The photograph was taken at an angle · the lesion is associated with pain, burning and itching · texture is reported as raised or bumpy and rough or flaky · the patient indicates the condition has been present for one to four weeks · the affected area is the back of the hand: 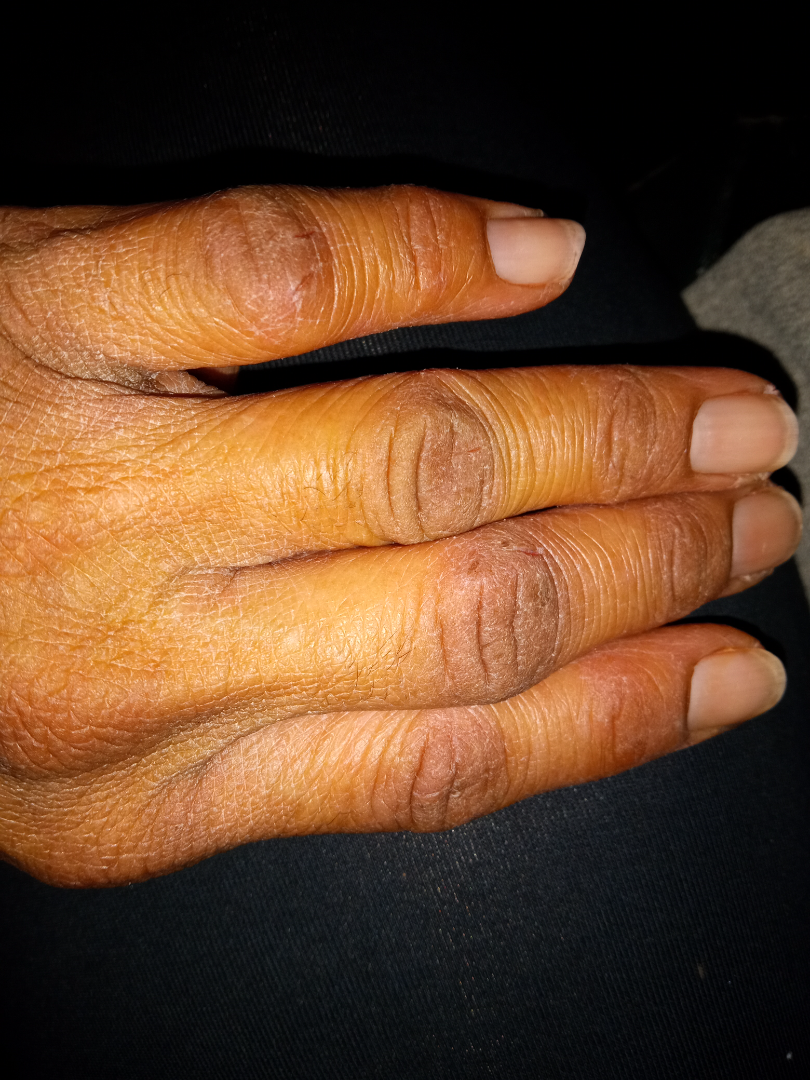Most likely Eczema.